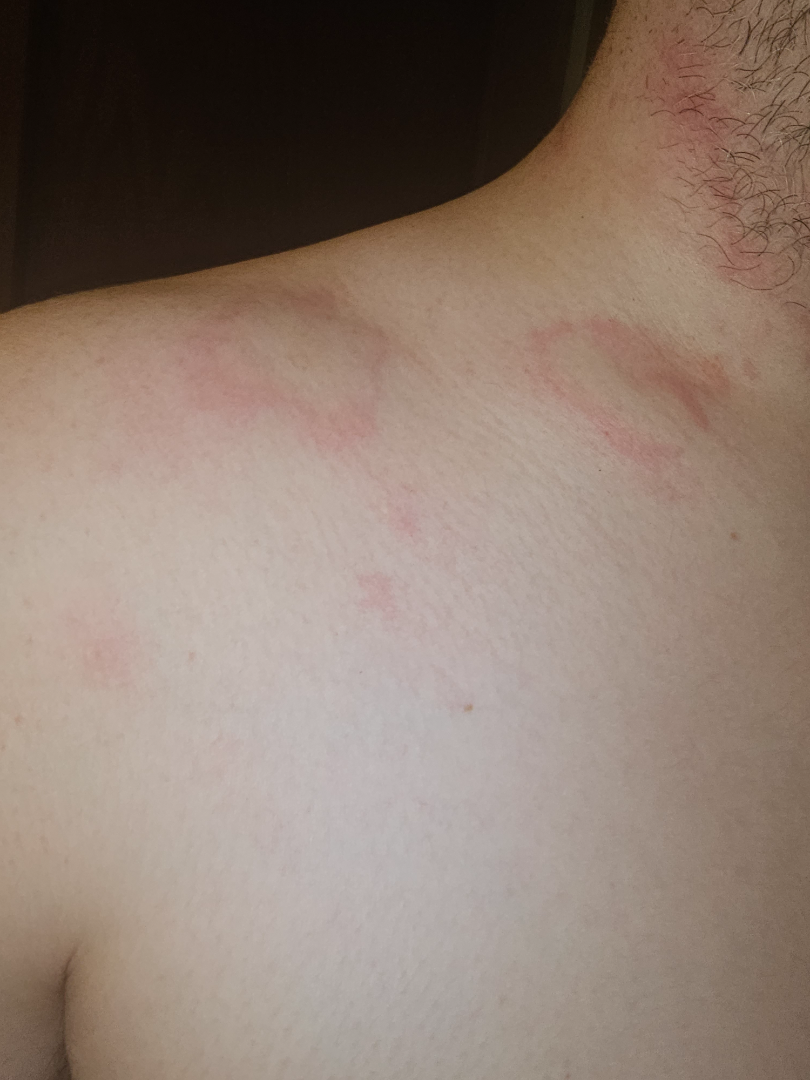Q: What is the framing?
A: at a distance
Q: Anatomic location?
A: head or neck
Q: What conditions are considered?
A: Tinea, Pityriasis rosea and Allergic Contact Dermatitis were considered with similar weight